The patient is Fitzpatrick phototype II; a clinical photograph showing a skin lesion; a male subject aged 79.
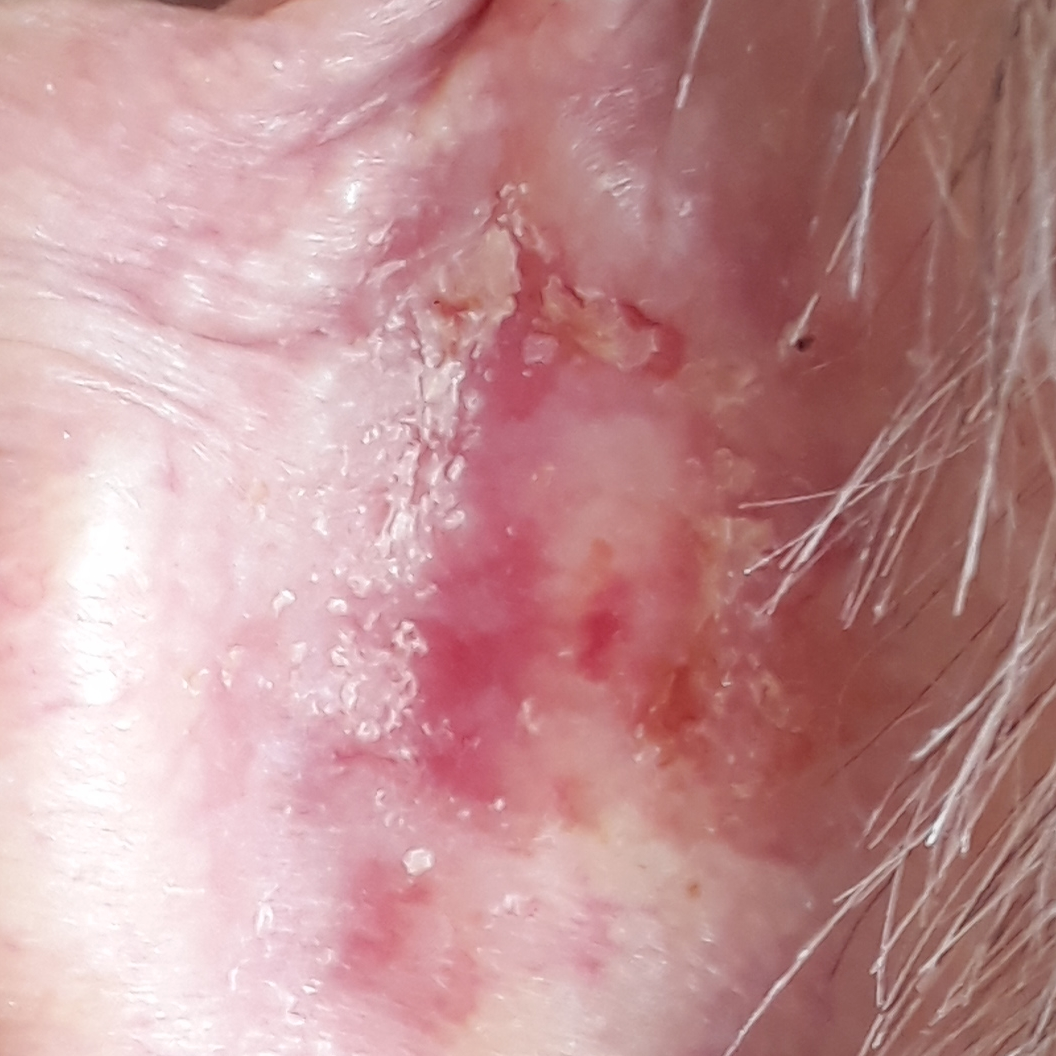The lesion measures approximately 30 × 15 mm. The patient reports that the lesion itches, has bled, is elevated, and hurts. Histopathology confirmed a basal cell carcinoma.